Close-up view. Reported lesion symptoms include enlargement and itching. The front of the torso, back of the hand and arm are involved. The lesion is described as raised or bumpy and rough or flaky. Present for three to twelve months.
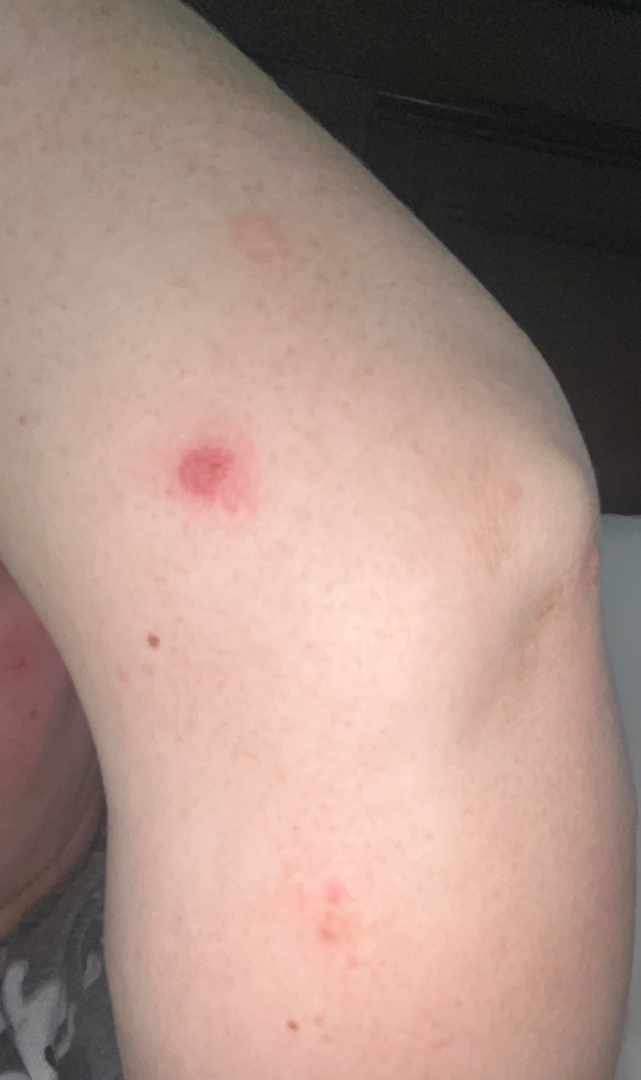<report>
  <differential>
    <tied_lead>Impetigo; Photodermatitis; Acute dermatitis, NOS</tied_lead>
  </differential>
</report>